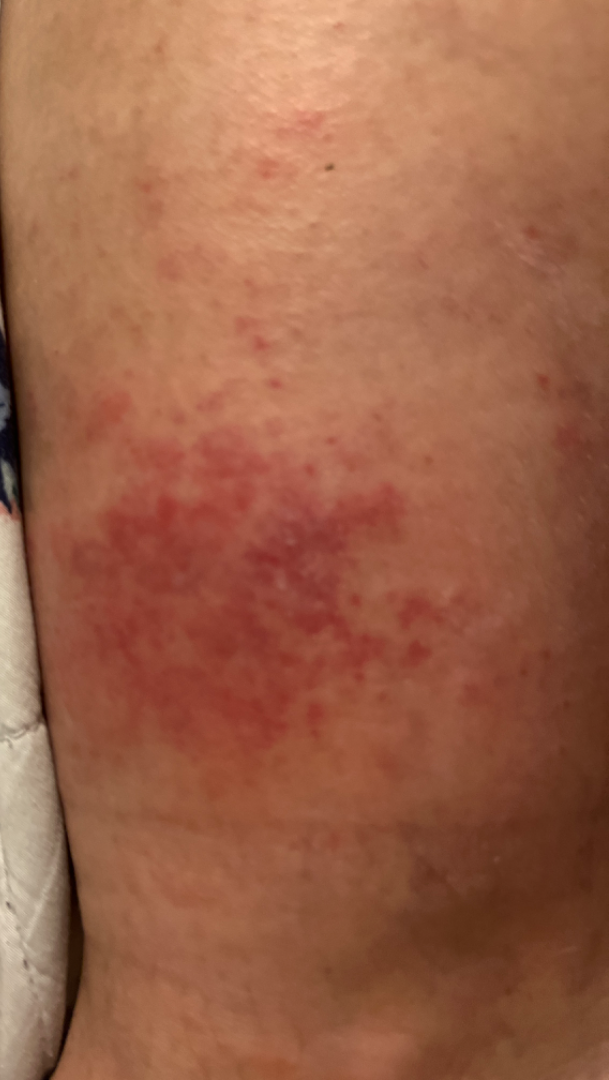<case>
  <differential>
    <leading>Stasis Dermatitis</leading>
  </differential>
</case>